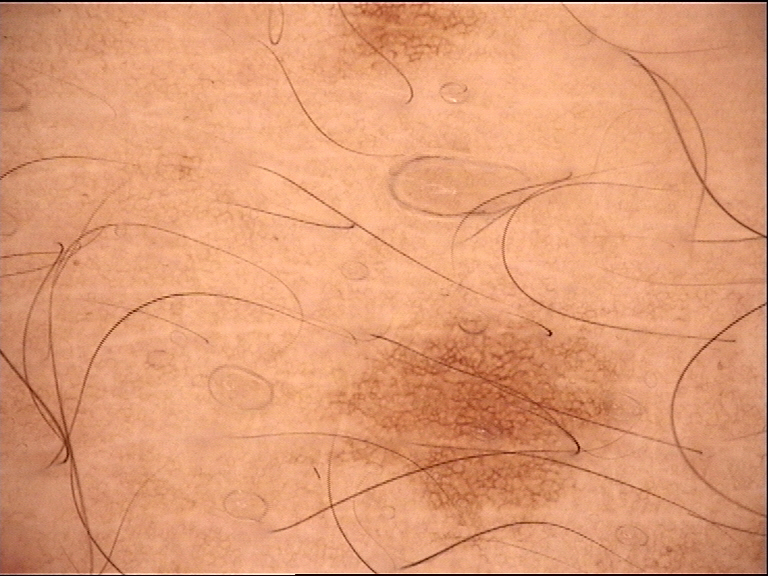Case:
* class: junctional nevus (expert consensus)